A dermoscopic image of a skin lesion · the patient is a female about 25 years old.
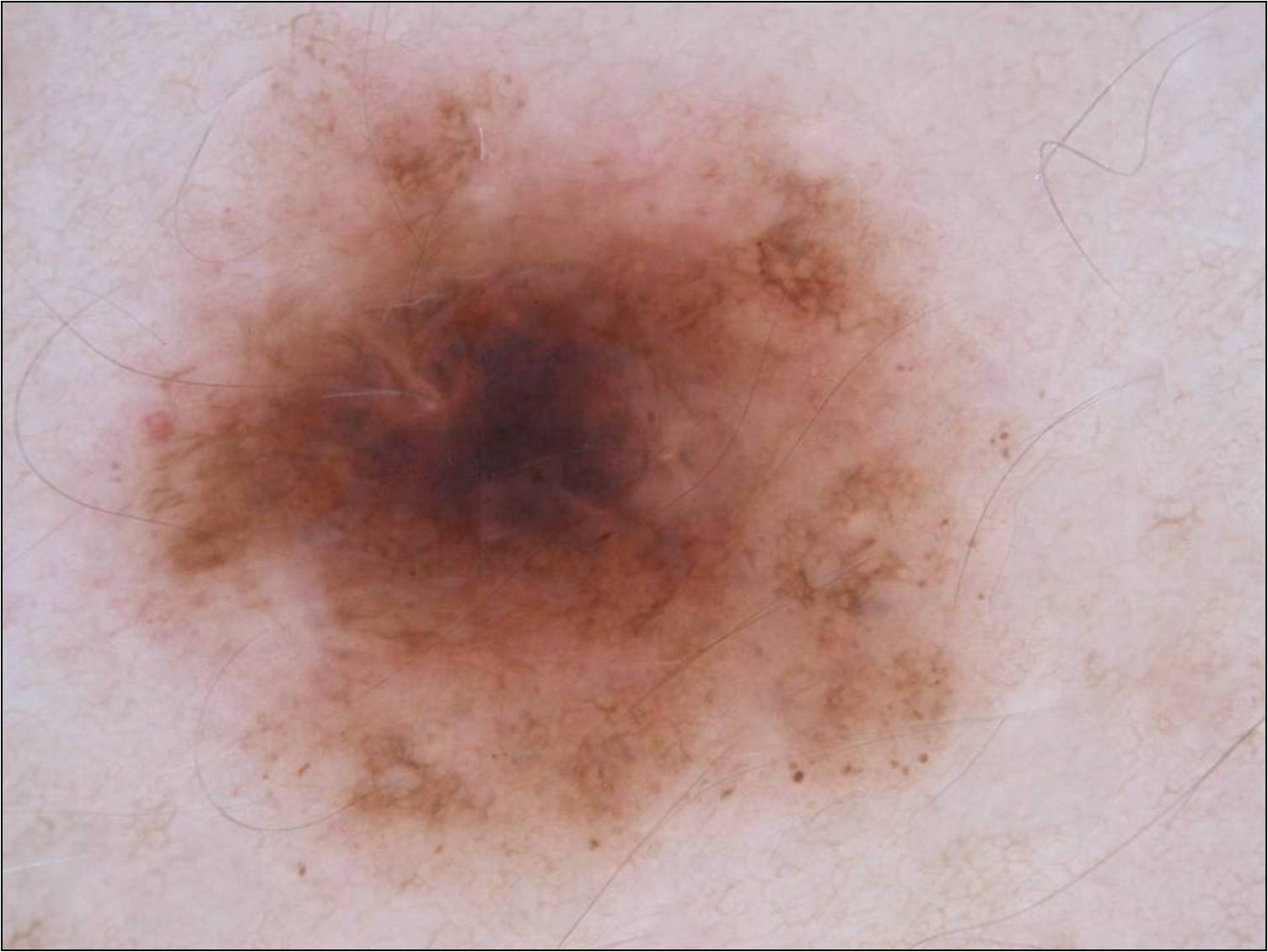<dermoscopy>
  <dermoscopic_features>
    <present>globules, pigment network</present>
    <absent>negative network, milia-like cysts, streaks</absent>
  </dermoscopic_features>
  <lesion_location>
    <bbox_xyxy>54, 15, 1033, 928</bbox_xyxy>
  </lesion_location>
  <lesion_extent>
    <approx_field_fraction_pct>51</approx_field_fraction_pct>
  </lesion_extent>
  <diagnosis>
    <name>melanocytic nevus</name>
    <malignancy>benign</malignancy>
    <lineage>melanocytic</lineage>
    <provenance>clinical</provenance>
  </diagnosis>
</dermoscopy>